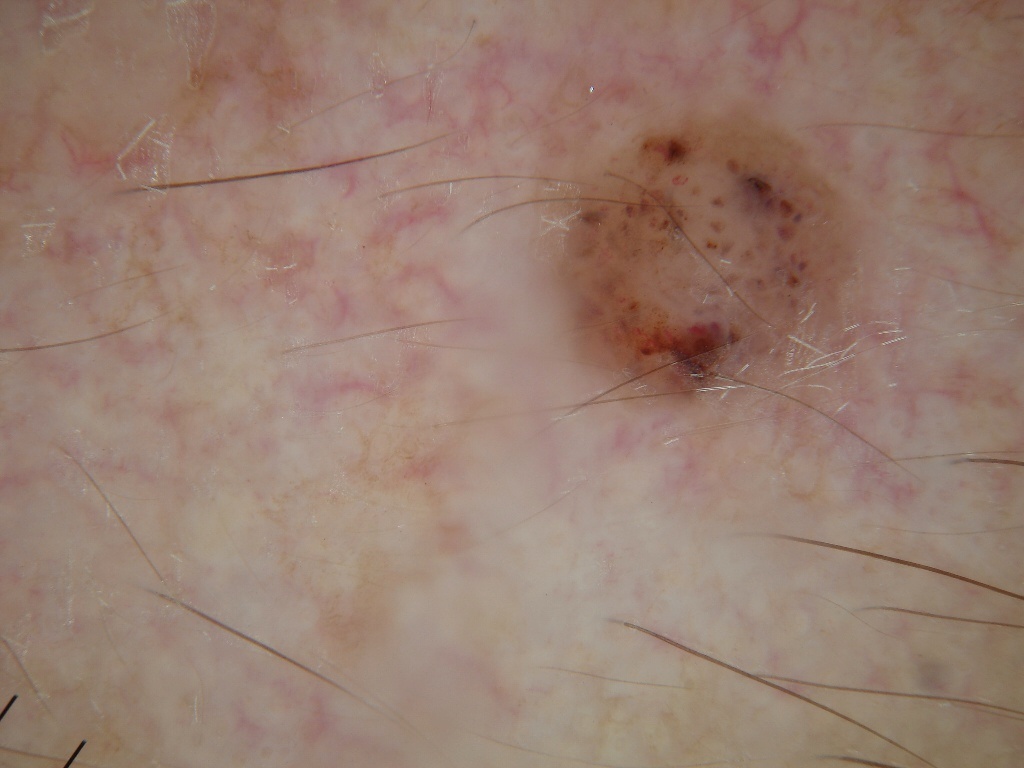A male subject aged 63-67. A dermoscopy image of a single skin lesion. The lesion occupies the region <box>536, 92, 868, 434</box>. On dermoscopy, the lesion shows no negative network, streaks, globules, pigment network, or milia-like cysts. Histopathology confirmed a melanoma.